A dermoscopic image of a skin lesion.
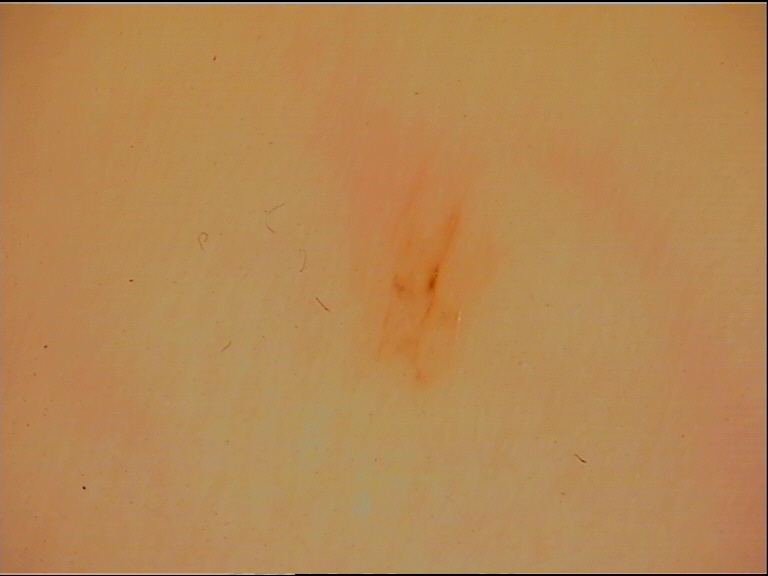Summary: This is a banal lesion. Conclusion: Labeled as an acral junctional nevus.